The chart documents a prior melanoma · Fitzpatrick skin type II.
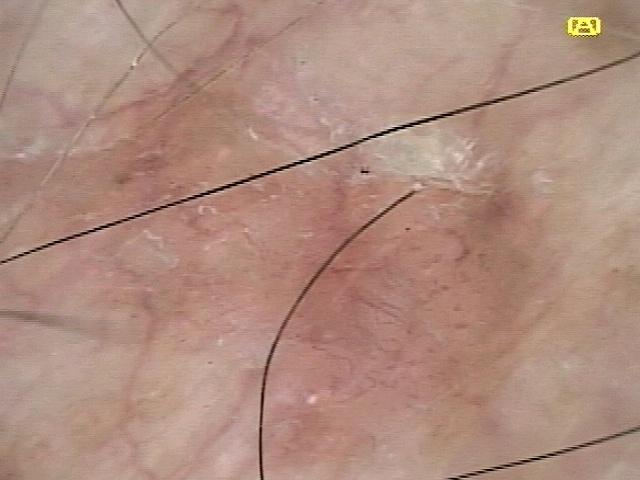anatomic site=the trunk
pathology=Basal cell carcinoma (biopsy-proven)